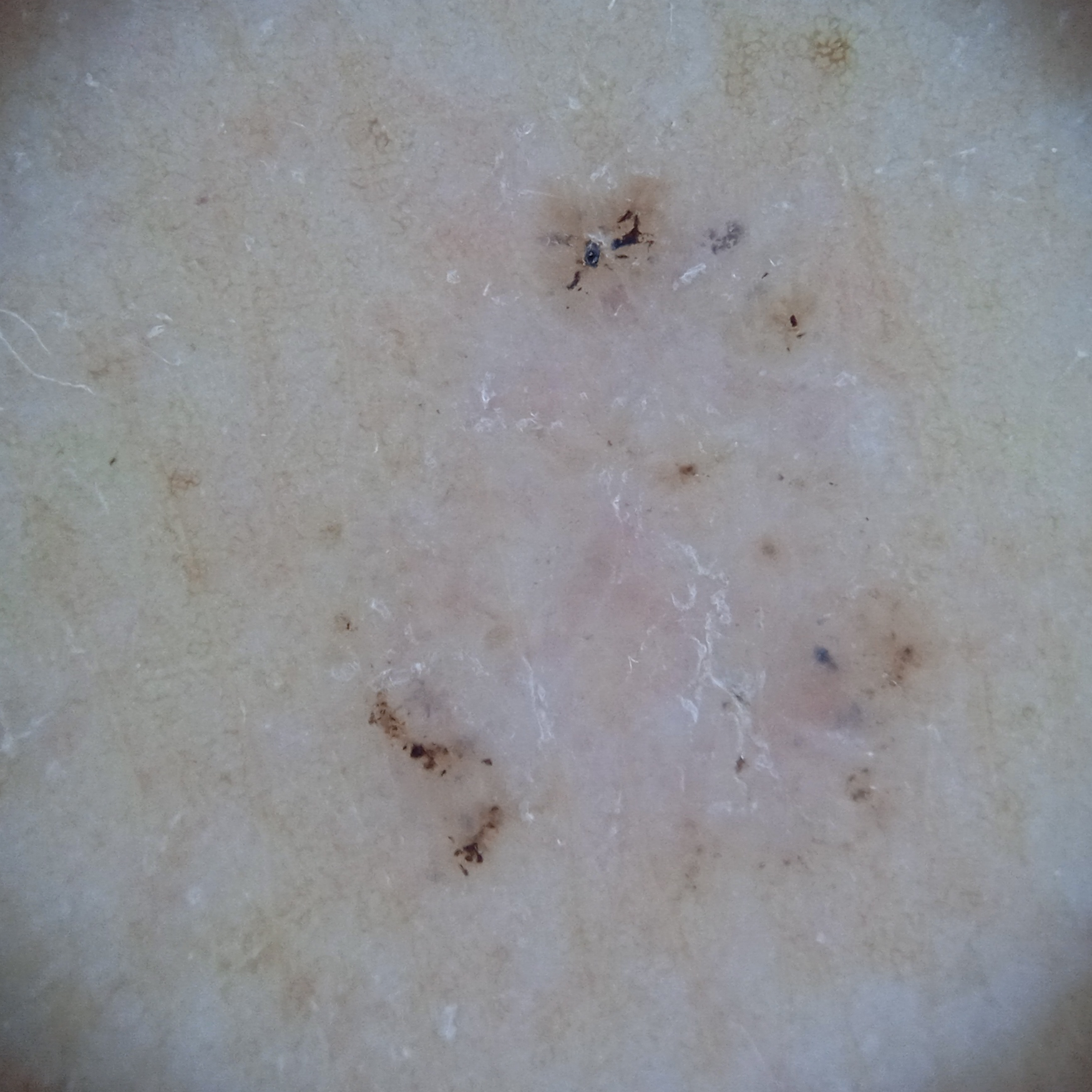A dermoscopic image of a skin lesion. The referring clinician suspected basal cell carcinoma. A female patient aged 60. By self-report, a personal history of skin cancer and a personal history of cancer. The patient says their skin tans without first burning. Measuring roughly 7.8 mm. The diagnostic impression was a basal cell carcinoma.